The contributor is 30–39, female; the lesion involves the leg; a close-up photograph — 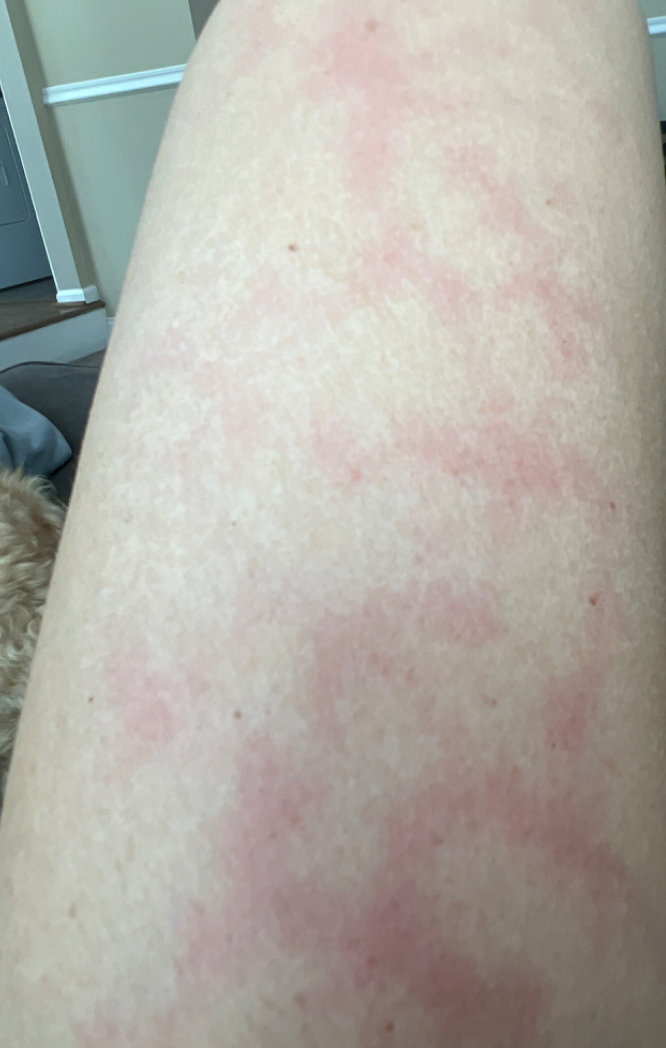present for=about one day
patient describes the issue as=skin that appeared healthy to them
described texture=flat
reported symptoms=none reported
other reported symptoms=none reported
assessment=the favored diagnosis is Livedo reticularis; an alternative is Erythema ab igne